A close-up photograph; the lesion involves the arm; reported lesion symptoms include itching and enlargement; the patient is female; the patient considered this a rash; the contributor reports the lesion is rough or flaky; non-clinician graders estimated Monk Skin Tone 3–4: 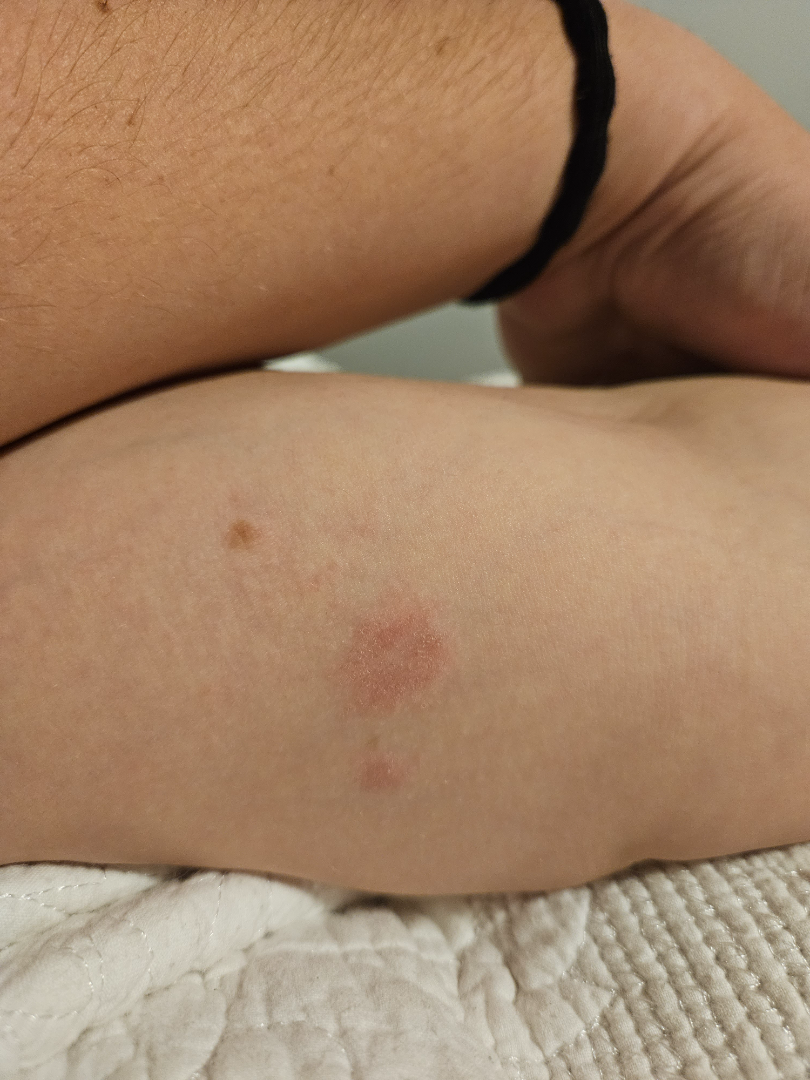Findings: On teledermatology review, the leading consideration is Eczema; also on the differential is Psoriasis; an alternative is Allergic Contact Dermatitis.